The photo was captured at an angle; male patient, age 60–69; the patient also reports joint pain; the lesion is associated with bothersome appearance, enlargement, pain and burning; the affected area is the arm; the lesion is described as rough or flaky, fluid-filled and raised or bumpy; the condition has been present for one to four weeks:
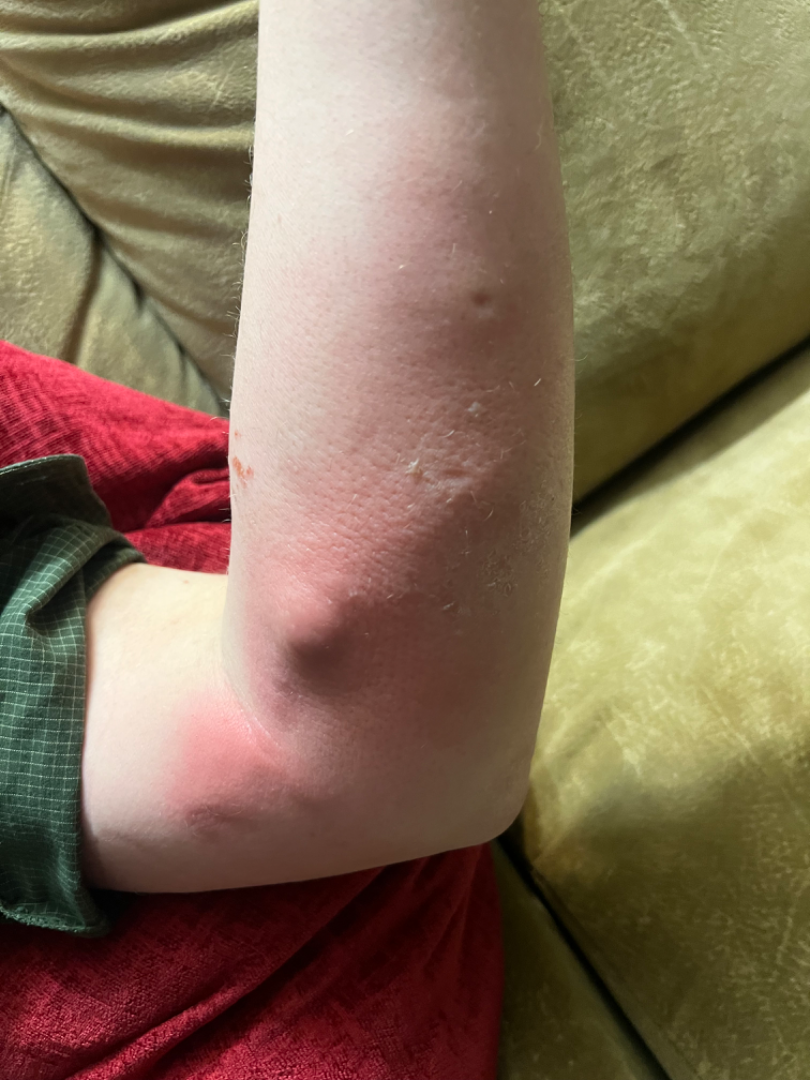Assessment:
On photographic review, the leading consideration is Abscess; possibly Cellulitis; less probable is Localised skin eruption due to drugs and medicaments; less likely is Lymphocutaneous sporotrichosis; a remote consideration is Cutaneous leishmaniasis.